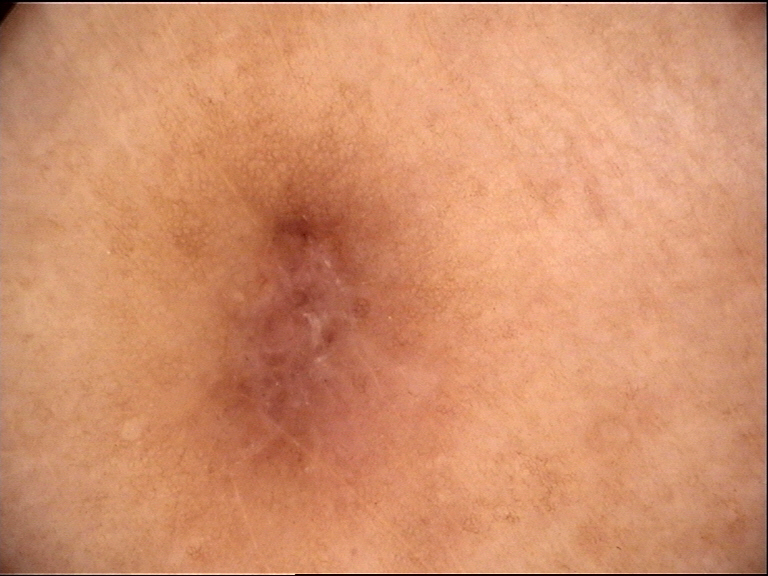assessment — dermatofibroma (expert consensus)